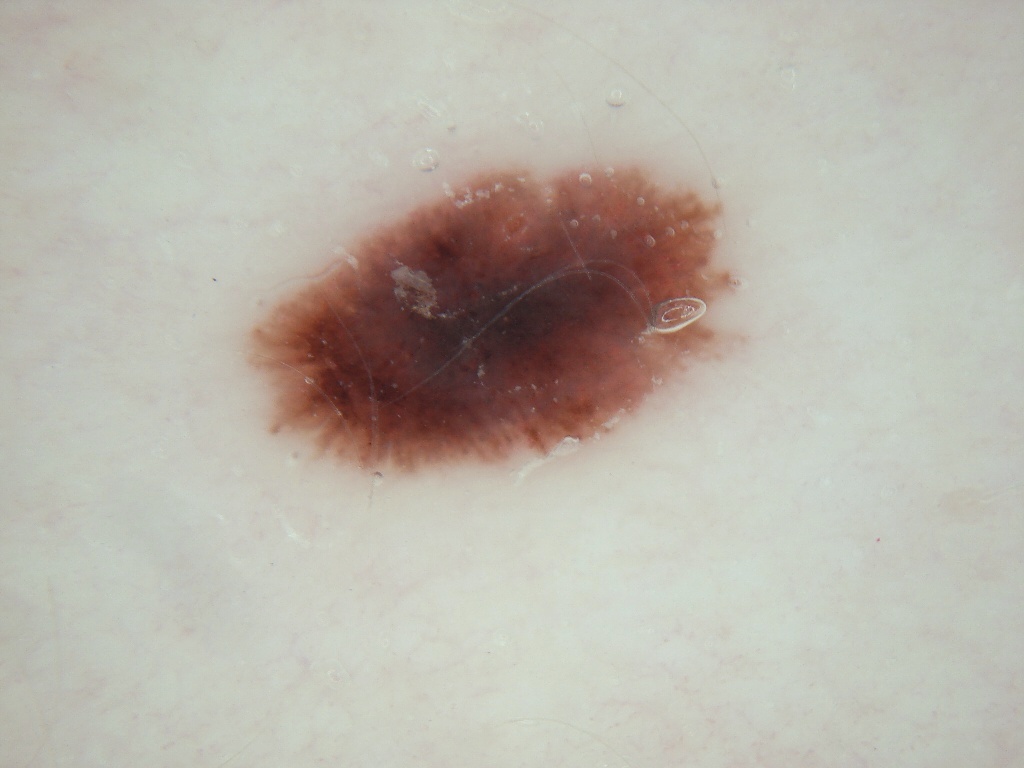{"image": {"modality": "dermoscopy"}, "patient": {"sex": "male", "age_approx": 30}, "dermoscopic_features": {"present": ["streaks"], "absent": ["milia-like cysts", "globules", "pigment network", "negative network"]}, "lesion_location": {"bbox_xyxy": [241, 154, 737, 476]}, "diagnosis": {"name": "melanoma", "malignancy": "malignant", "lineage": "melanocytic", "provenance": "histopathology"}}